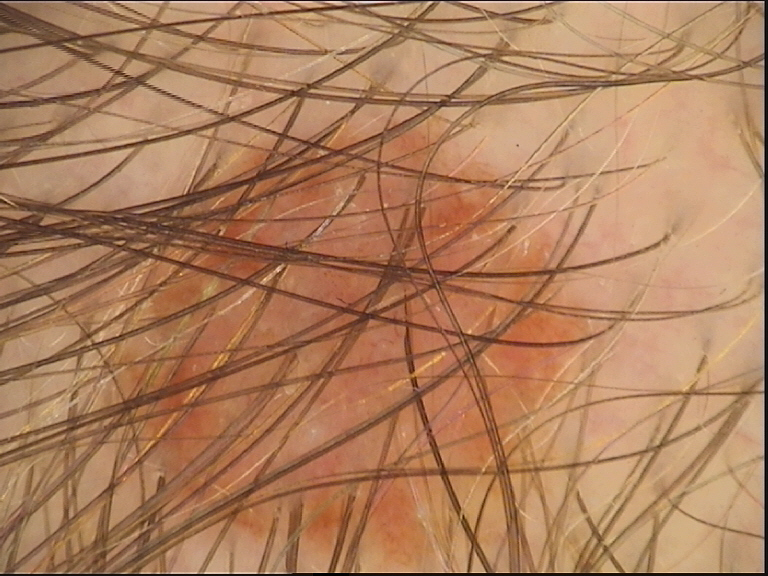{
  "image": "dermoscopy",
  "diagnosis": {
    "name": "compound nevus",
    "code": "cb",
    "malignancy": "benign",
    "super_class": "melanocytic",
    "confirmation": "expert consensus"
  }
}